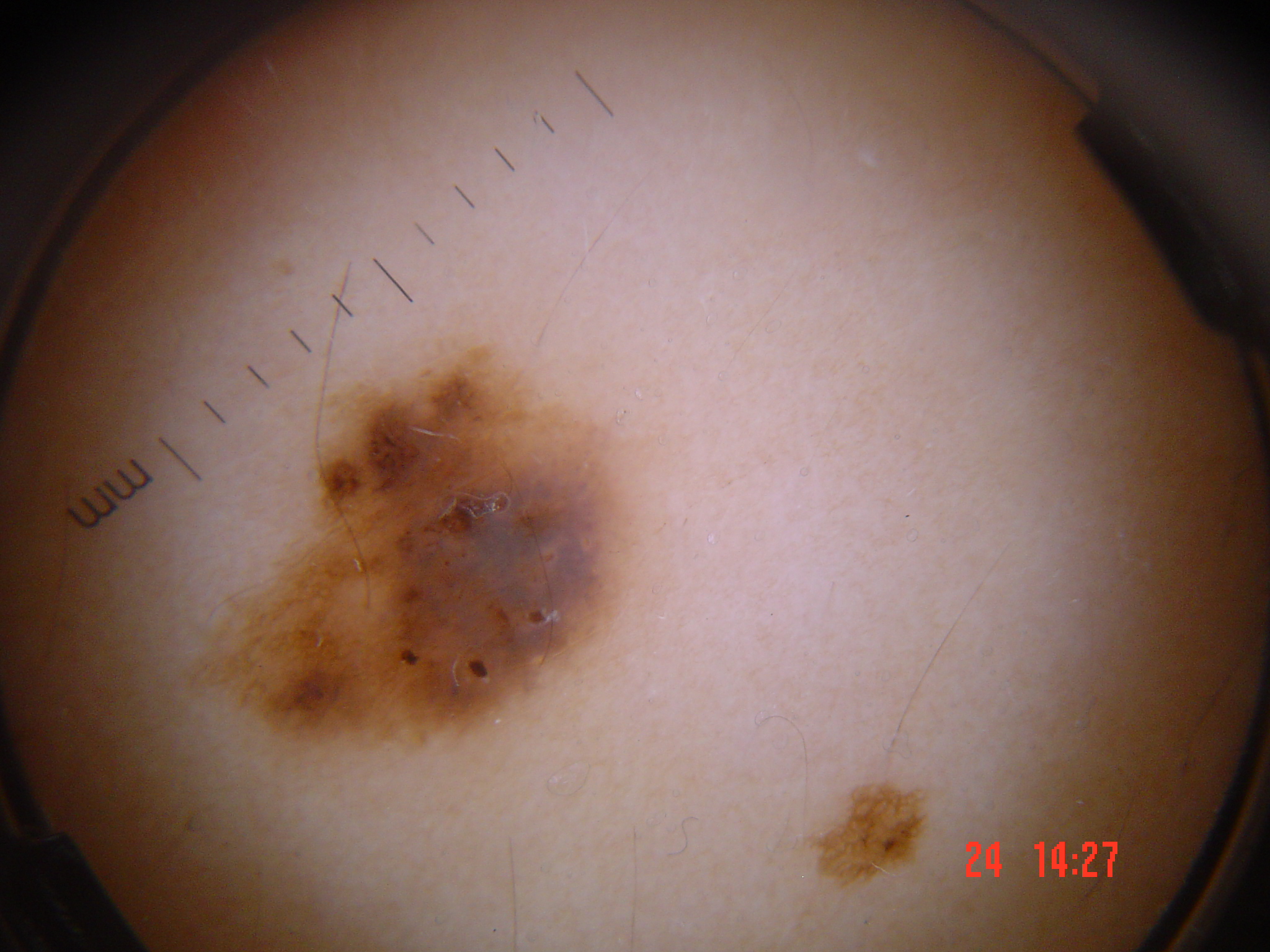Classified as a banal lesion — a congenital compound nevus.